A dermoscopic photograph of a skin lesion:
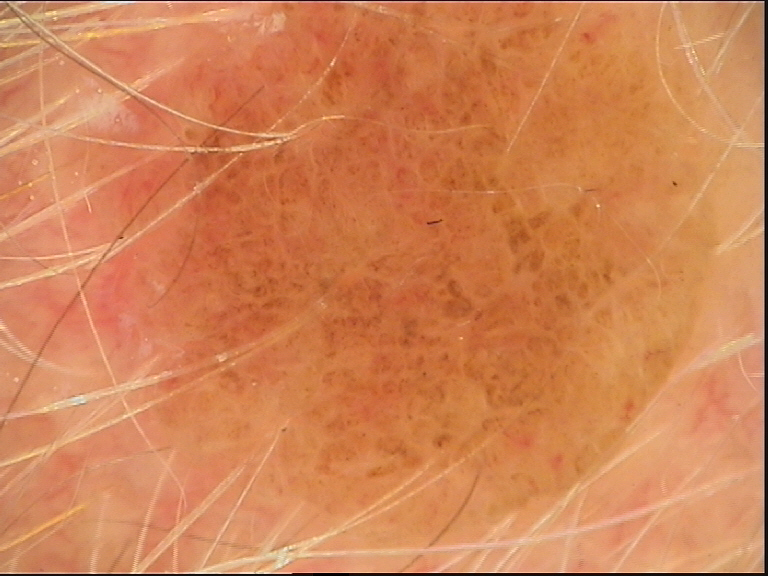The architecture is that of a banal lesion.
Consistent with a compound nevus.